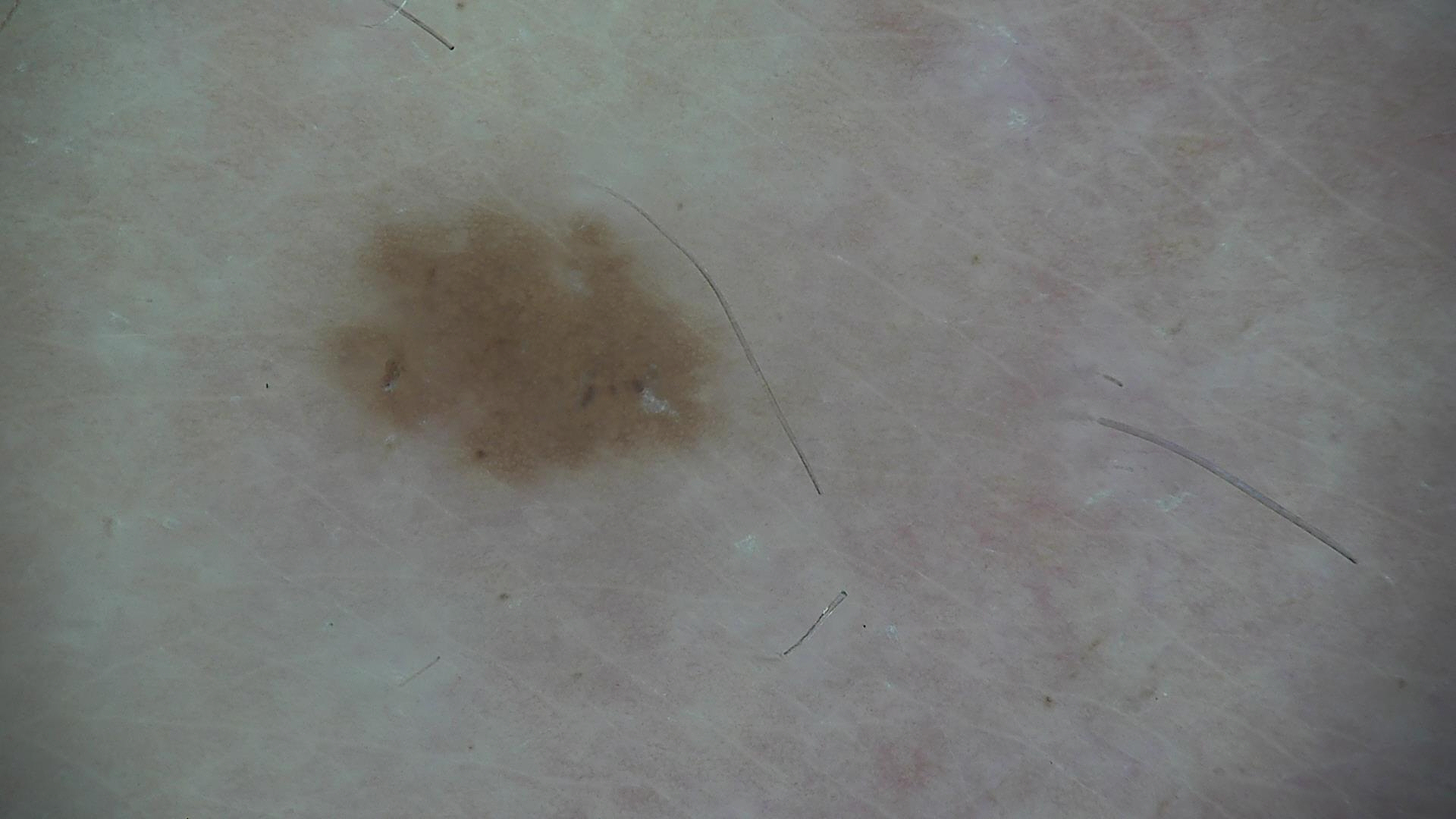Findings:
A dermoscopy image of a single skin lesion.
Conclusion:
Labeled as a benign lesion — a dysplastic junctional nevus.